Human graders estimated Monk Skin Tone 2 or 3 (two reviewer pools). The contributor is 50–59, male. The leg is involved. The patient considered this a rash. This image was taken at an angle. Reported lesion symptoms include bleeding and itching. The patient also reports fatigue, shortness of breath and mouth sores. The lesion is described as fluid-filled. Present for one to four weeks — 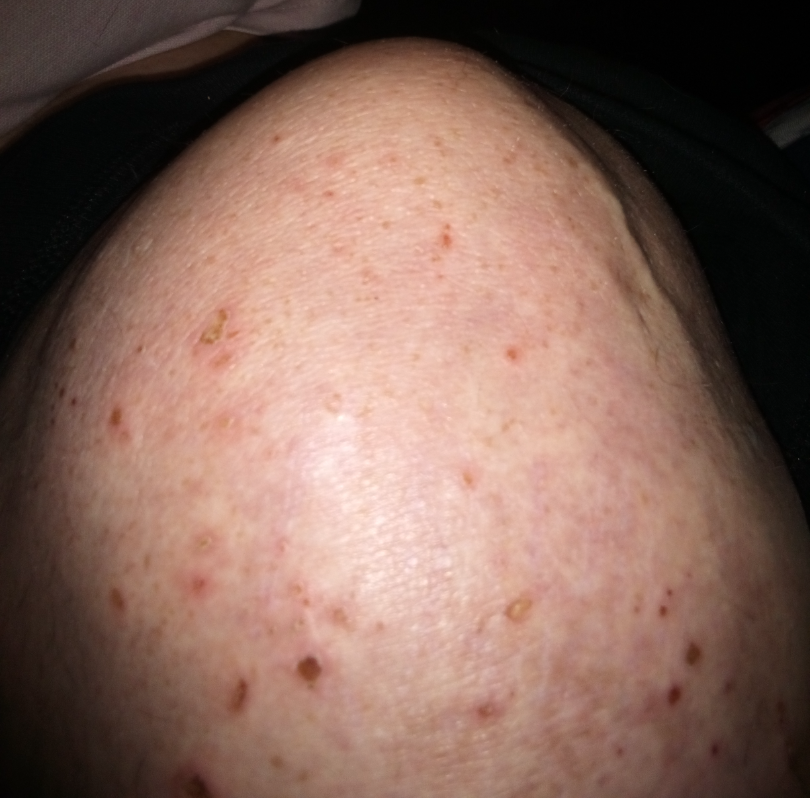<case>
<assessment>not assessable</assessment>
</case>